The patient is 40–49, female · no associated systemic symptoms reported · skin tone: self-reported FST I · the lesion involves the back of the hand, arm and leg · the lesion is described as rough or flaky · the photograph was taken at an angle.
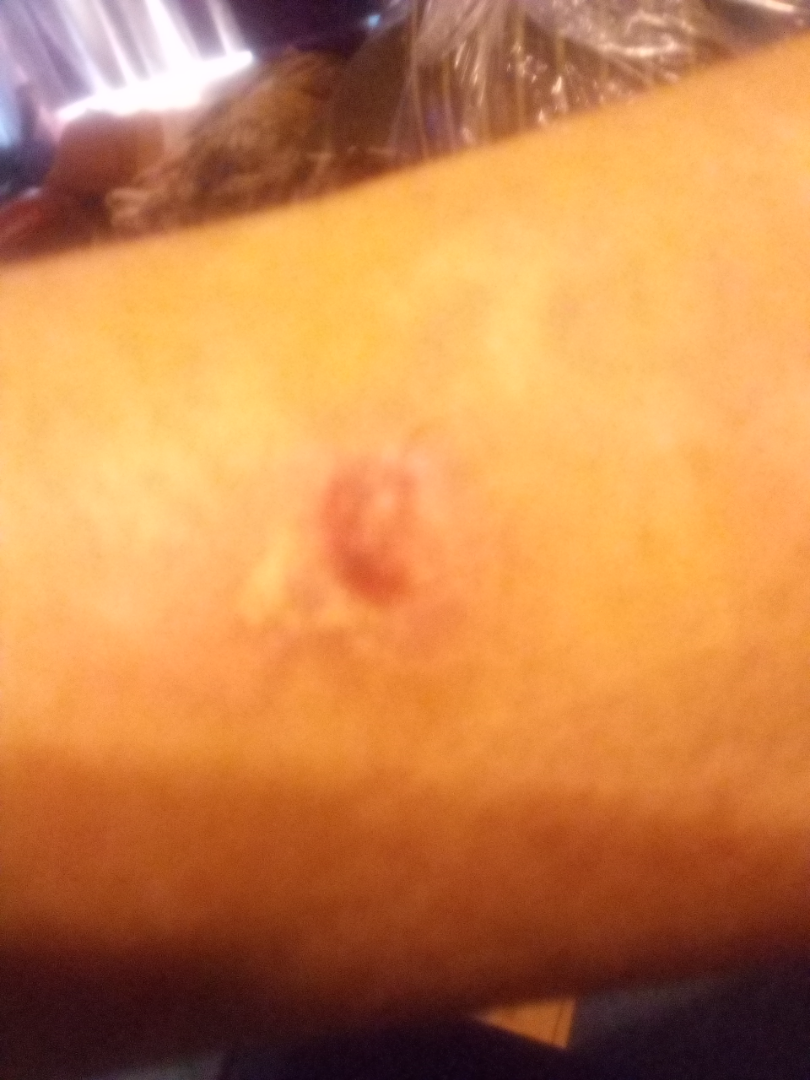Findings: The image was not sufficient for the reviewer to characterize the skin condition.